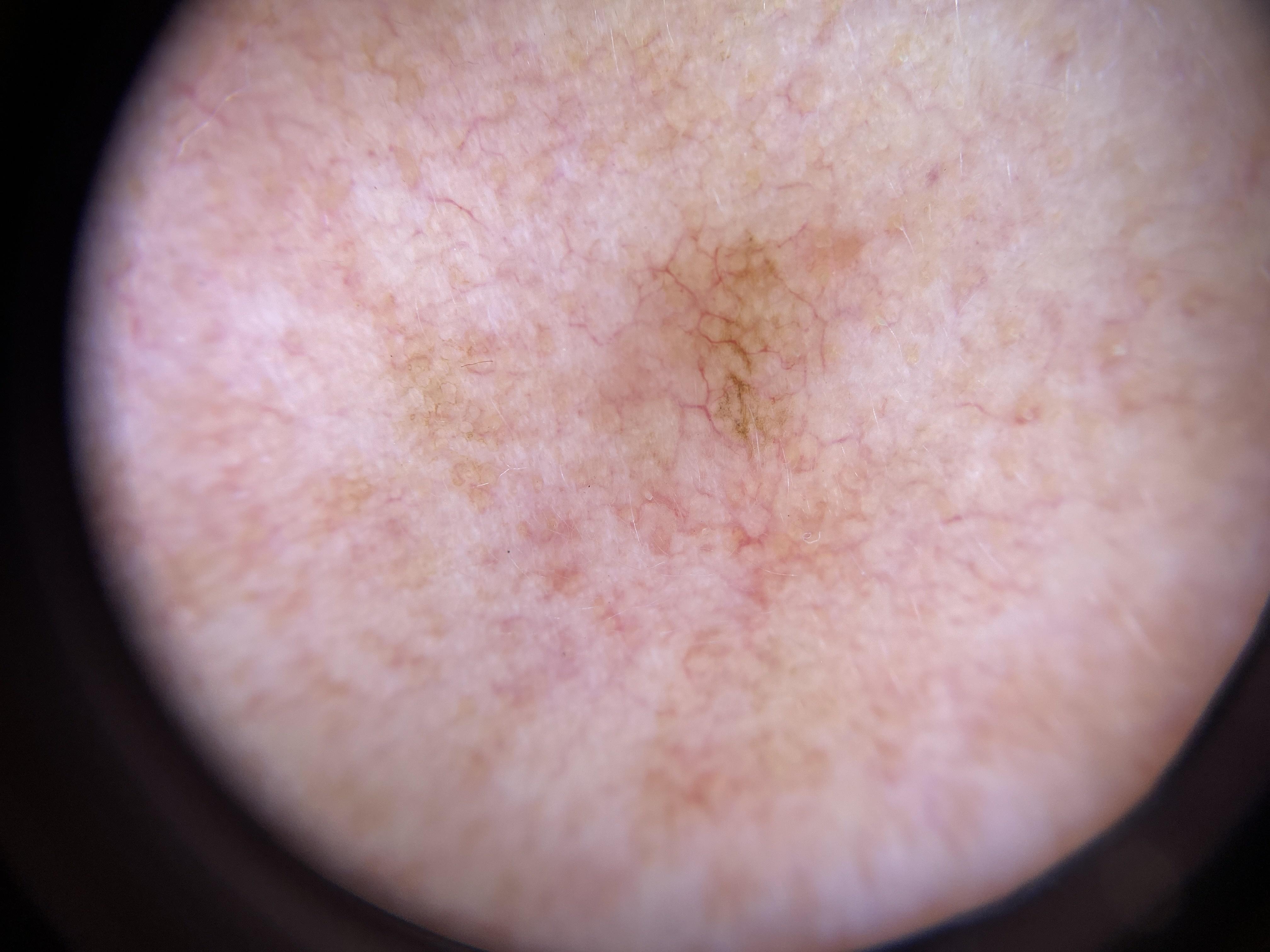Q: What is the diagnosis?
A: Solar lentigo (clinical impression)